Symptoms reported: itching. The affected area is the head or neck. A close-up photograph. The condition has been present for one to four weeks:
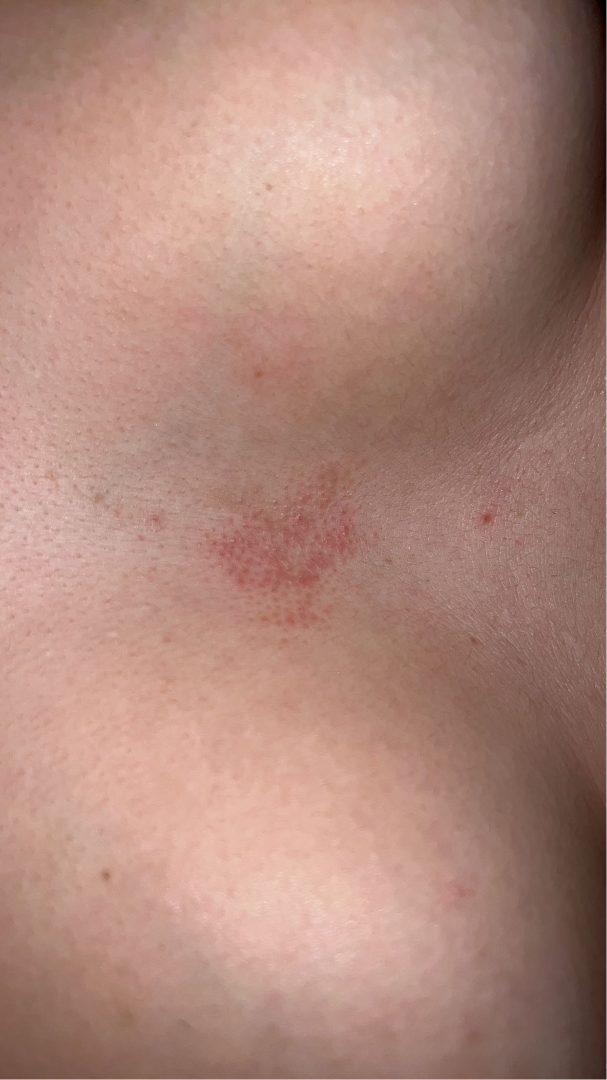Findings:
The reviewing dermatologist's impression was: Irritant Contact Dermatitis (favored); Eczema (considered).